A male subject aged 43. A clinical close-up photograph of a skin lesion: 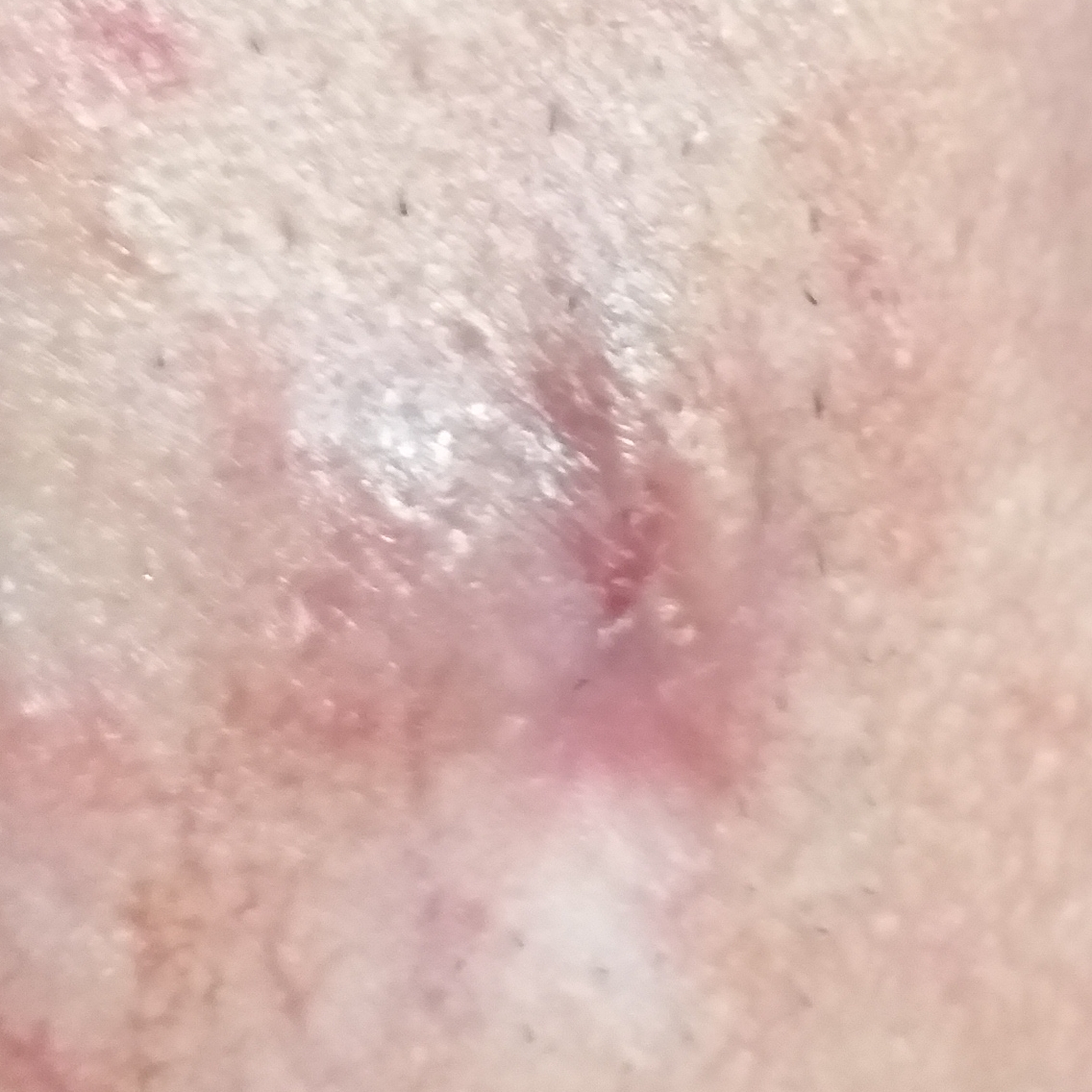Findings:
• location — the face
• reported symptoms — bleeding, growth, itching, elevation / no pain, no change in appearance
• diagnostic label — basal cell carcinoma (biopsy-proven)